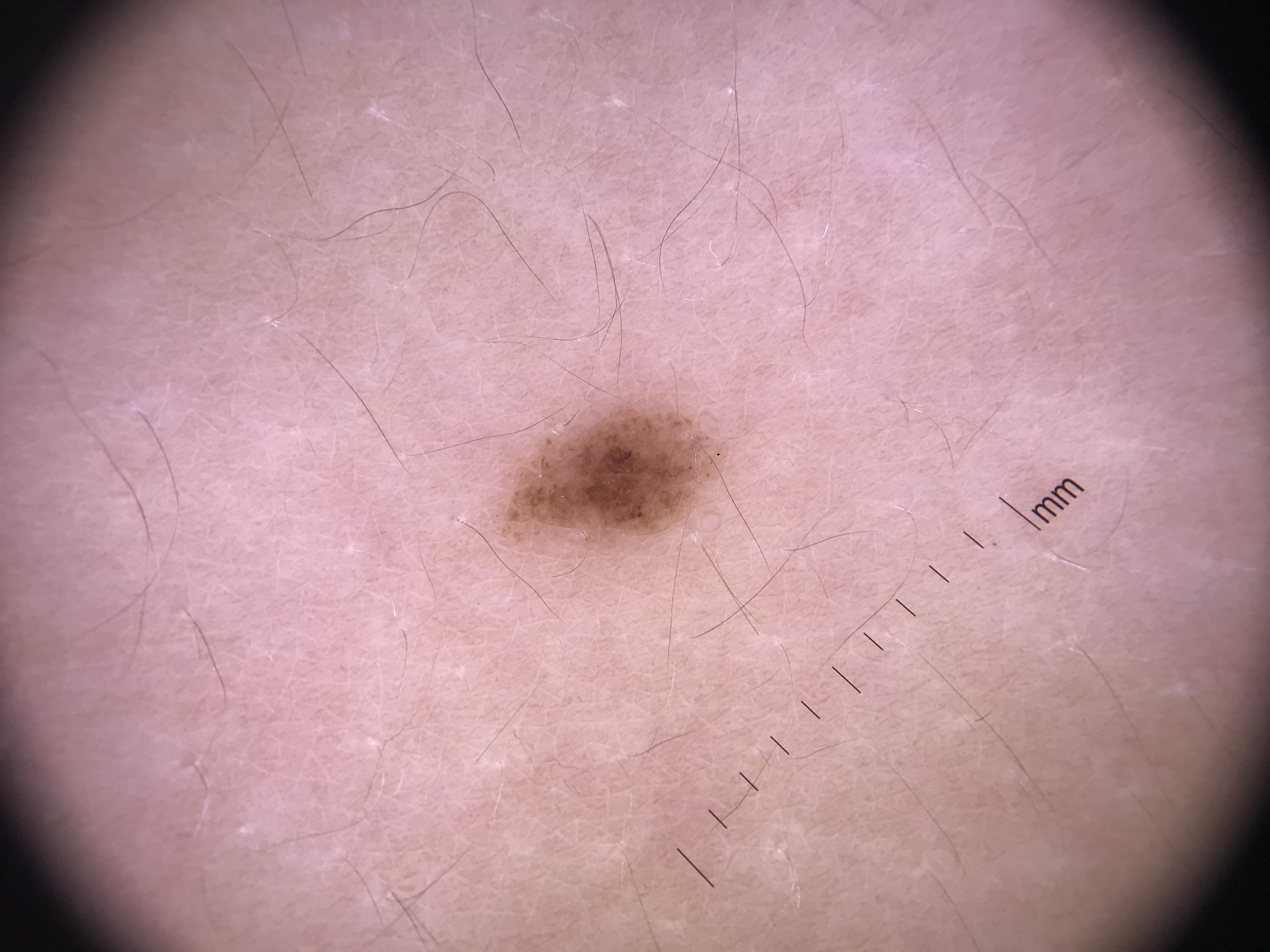image type — dermatoscopy; subtype — banal; assessment — junctional nevus (expert consensus).